The condition has been present for one to four weeks. Skin tone: Fitzpatrick skin type III; lay graders estimated Monk skin tone scale 2 or 5. The photograph is a close-up of the affected area. The patient is a female aged 18–29. The patient notes the lesion is flat. The lesion involves the head or neck, back of the torso, leg, arm and front of the torso. The patient did not report lesion symptoms — 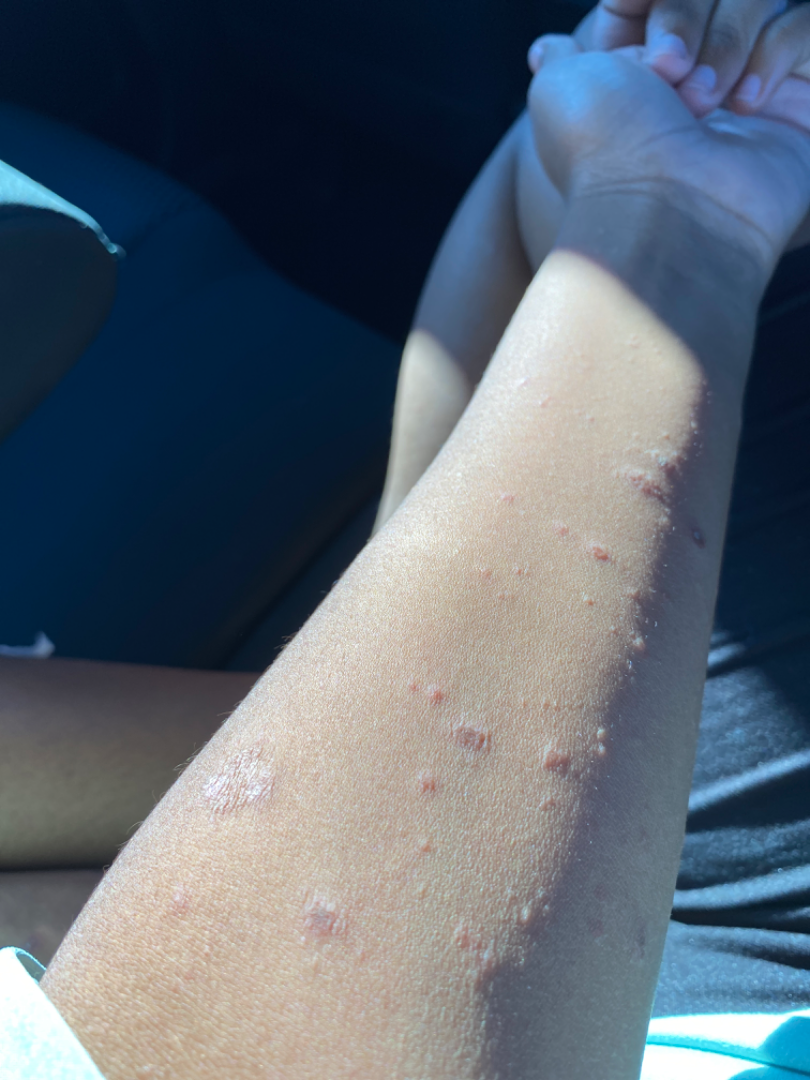Q: What conditions are considered?
A: one reviewing dermatologist: most consistent with Psoriasis; with consideration of Eczema; an alternative is Pityriasis lichenoides